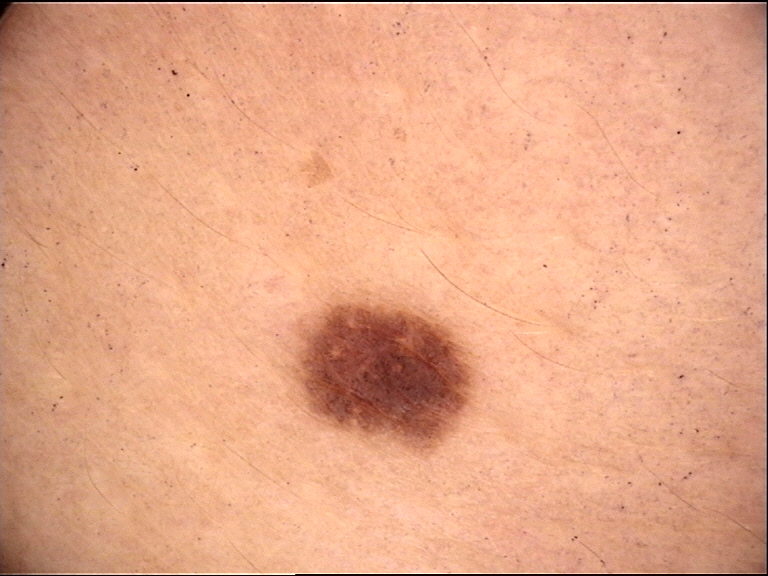Case: A dermoscopic image of a skin lesion. Conclusion: Diagnosed as a benign lesion — a dysplastic junctional nevus.